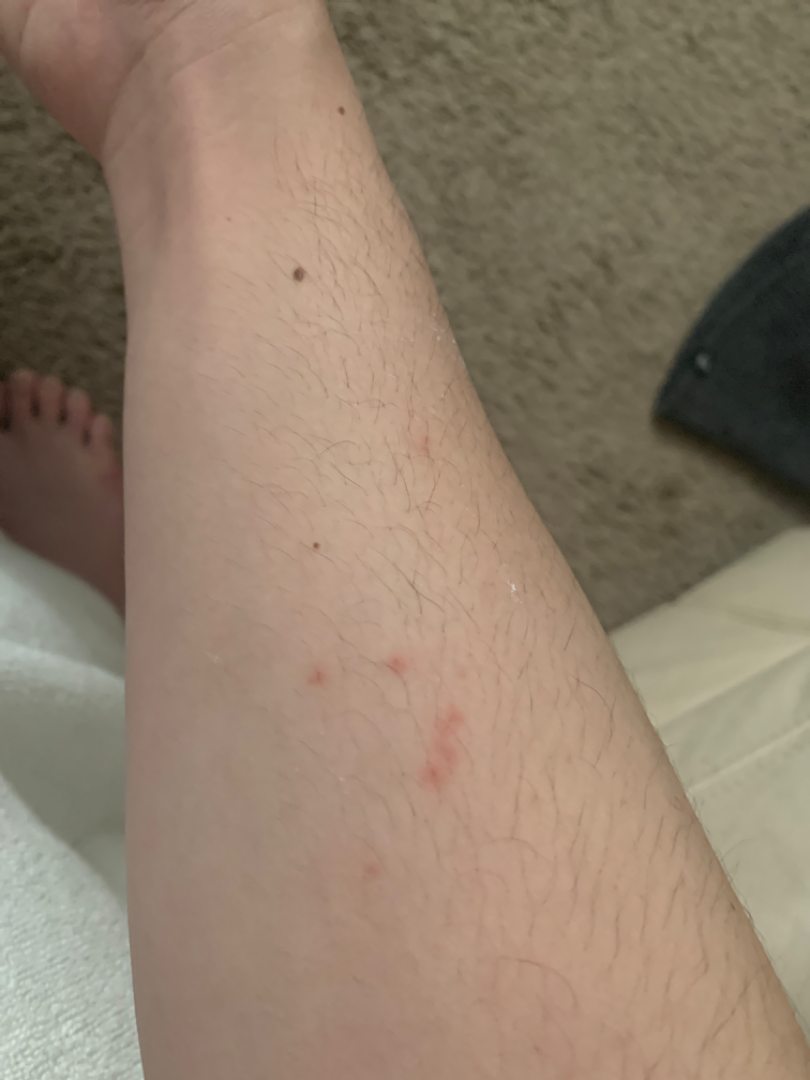* assessment · ungradable on photographic review
* image framing · close-up